The patient reports the condition has been present for less than one week. The patient is a female aged 40–49. Close-up view. Symptoms reported: bothersome appearance, itching and enlargement. The lesion is described as fluid-filled. Self-categorized by the patient as a rash. Located on the back of the hand.
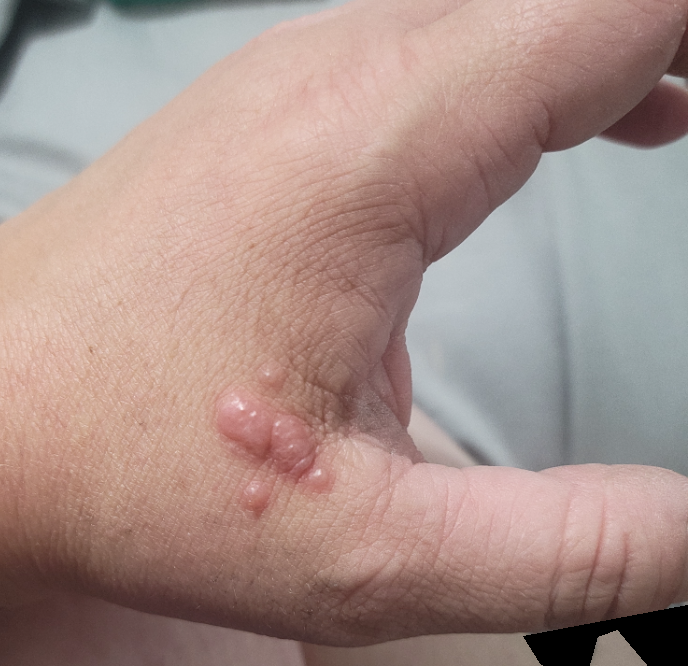  assessment: ungradable on photographic review